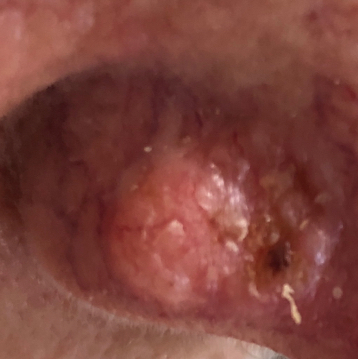{
  "skin_type": "II",
  "image": "clinical photo",
  "lesion_location": "the nose",
  "symptoms": {
    "present": [
      "elevation",
      "change in appearance",
      "bleeding",
      "growth"
    ]
  },
  "diagnosis": {
    "name": "basal cell carcinoma",
    "code": "BCC",
    "malignancy": "malignant",
    "confirmation": "histopathology"
  }
}